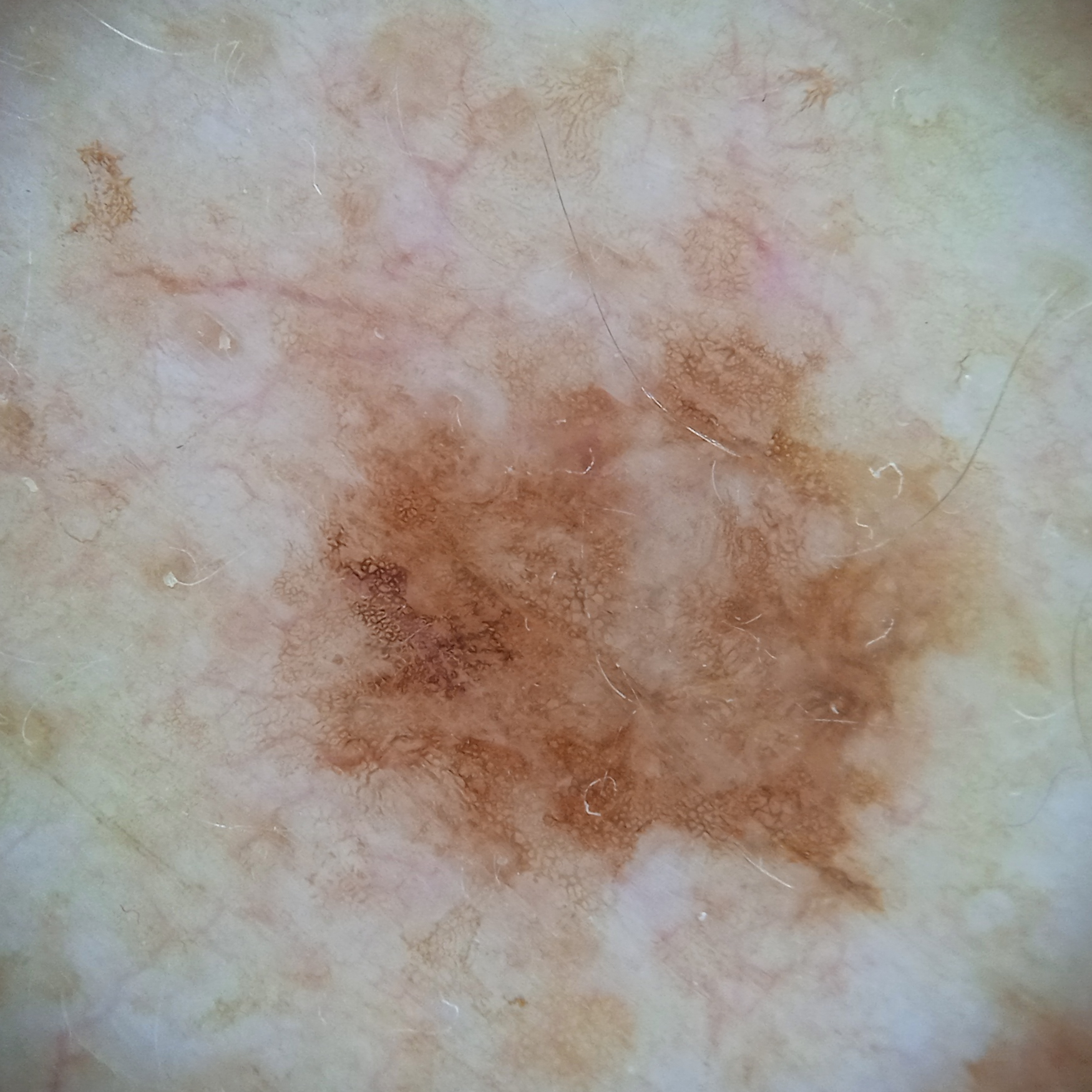The reviewing dermatologists could not reach a confident diagnosis. Case summary: A male patient age 81. Imaged for a research study, with no referral diagnosis recorded. A dermoscopic image of a skin lesion. The lesion is located on the back. The lesion measures approximately 8 mm.